A skin lesion imaged with a dermatoscope:
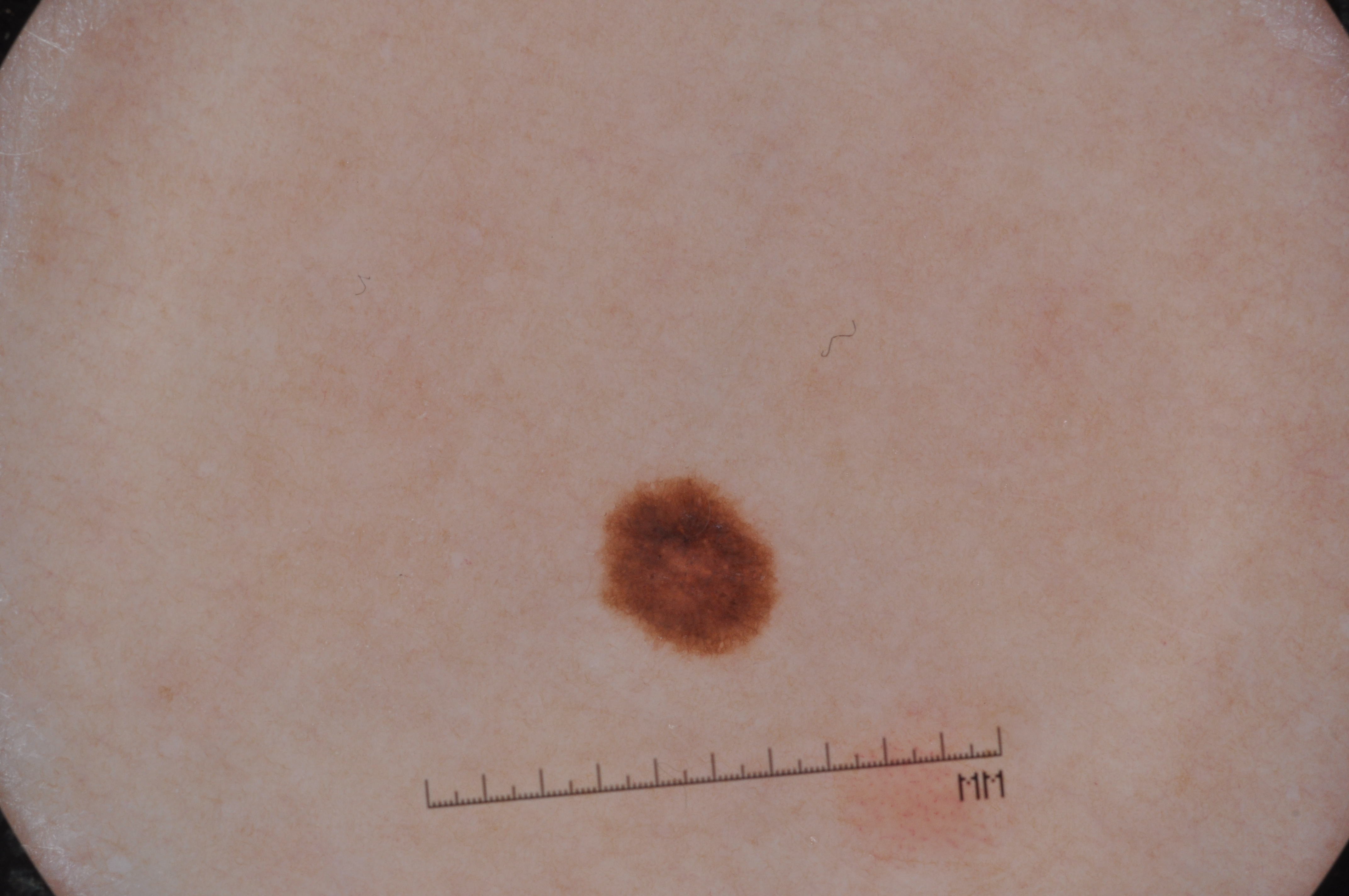Findings:
Dermoscopically, the lesion shows pigment network. The lesion's extent is 593 466 787 664.
Impression:
The diagnostic assessment was a melanocytic nevus, a benign lesion.